Contact-polarized dermoscopy of a skin lesion · a male patient in their mid- to late 70s.
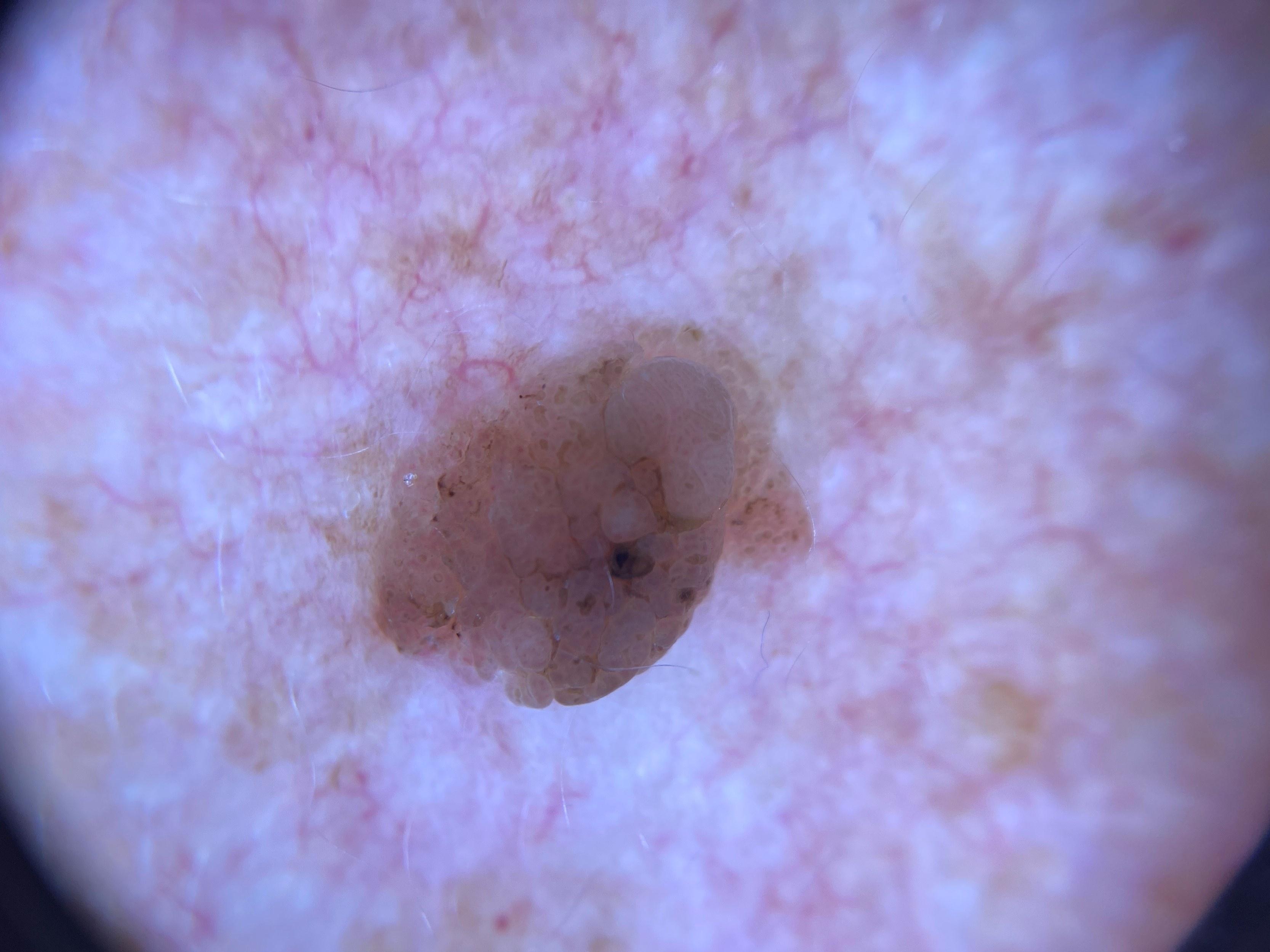The lesion is on the anterior trunk. Biopsy-confirmed as a seborrheic keratosis.